A female patient; a dermoscopy image of a single skin lesion:
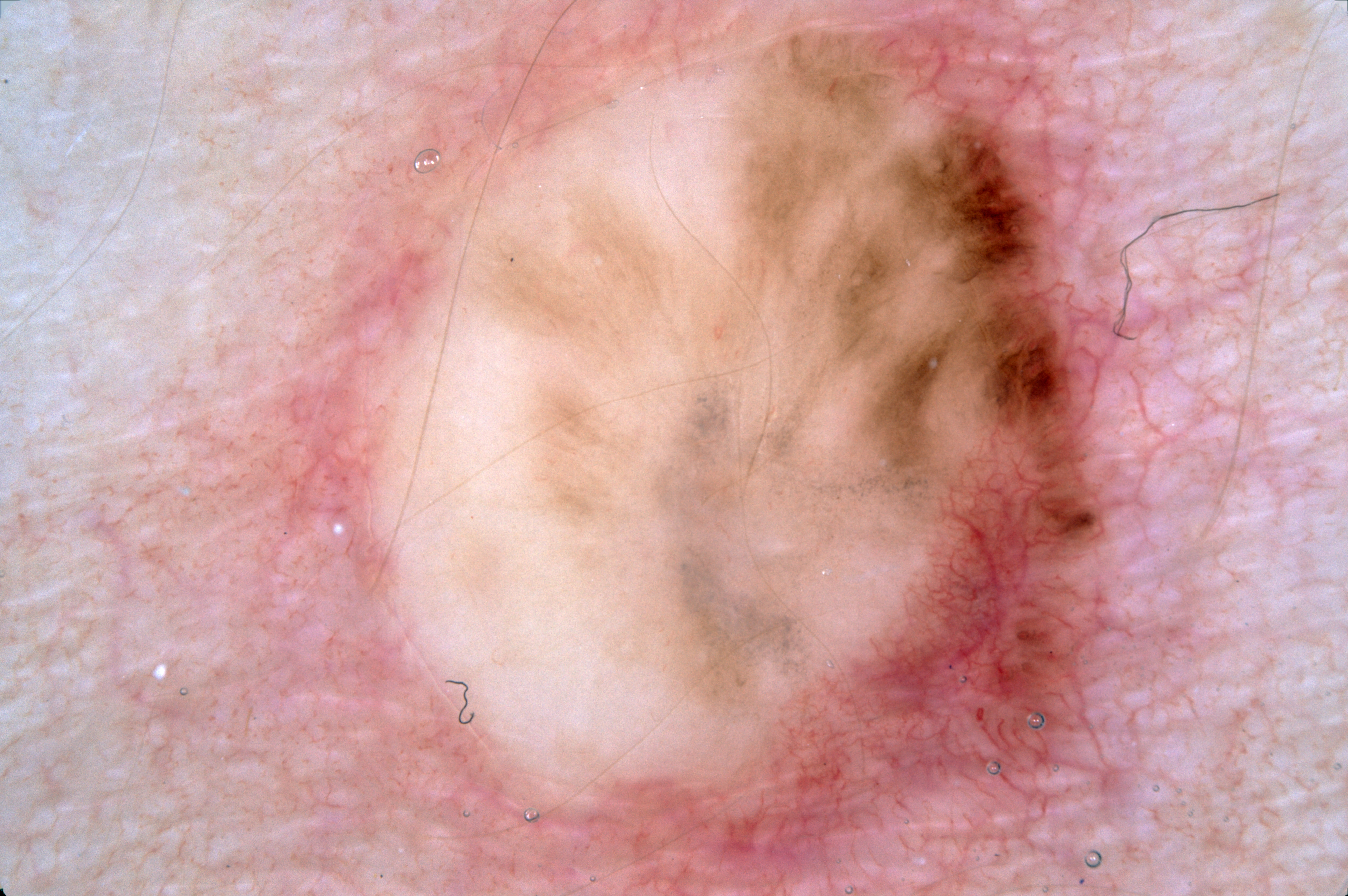absent dermoscopic findings = negative network, streaks, milia-like cysts, and pigment network; bounding box = 262, 3, 1178, 891; lesion extent = ~58% of the field; diagnosis = a melanocytic nevus, a benign skin lesion.